A dermoscopy image of a single skin lesion:
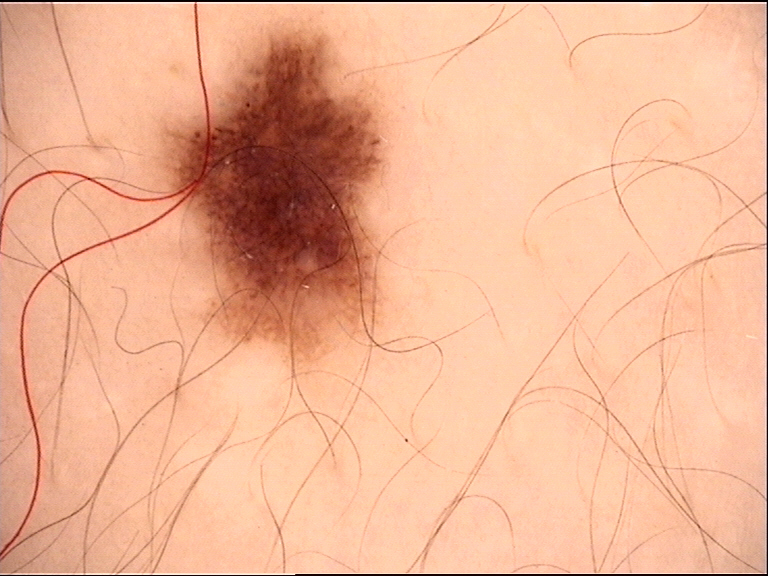class = dysplastic junctional nevus (expert consensus)